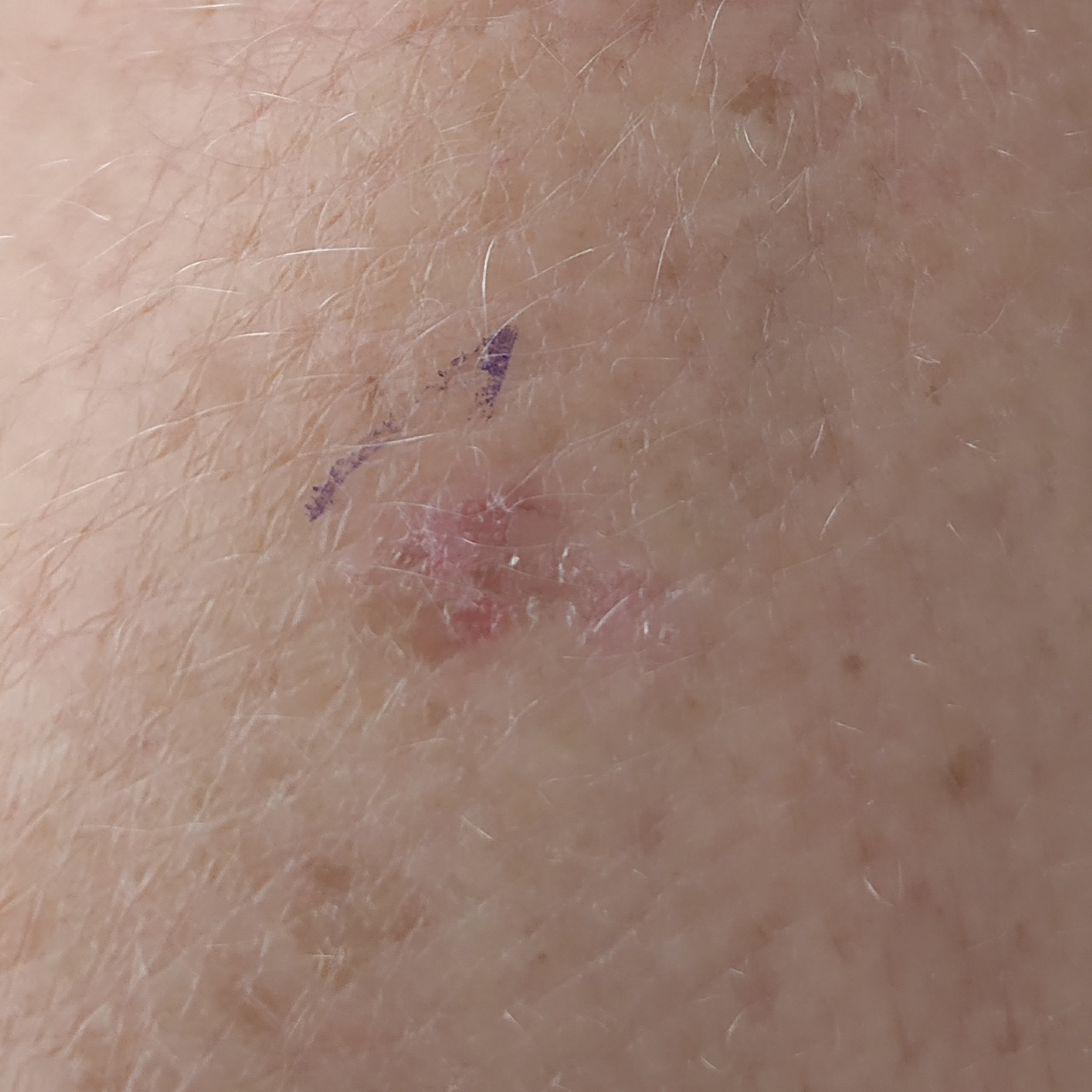The clinical impression was an actinic keratosis.